This image was taken at an angle. The affected area is the arm. Male contributor, age 50–59:
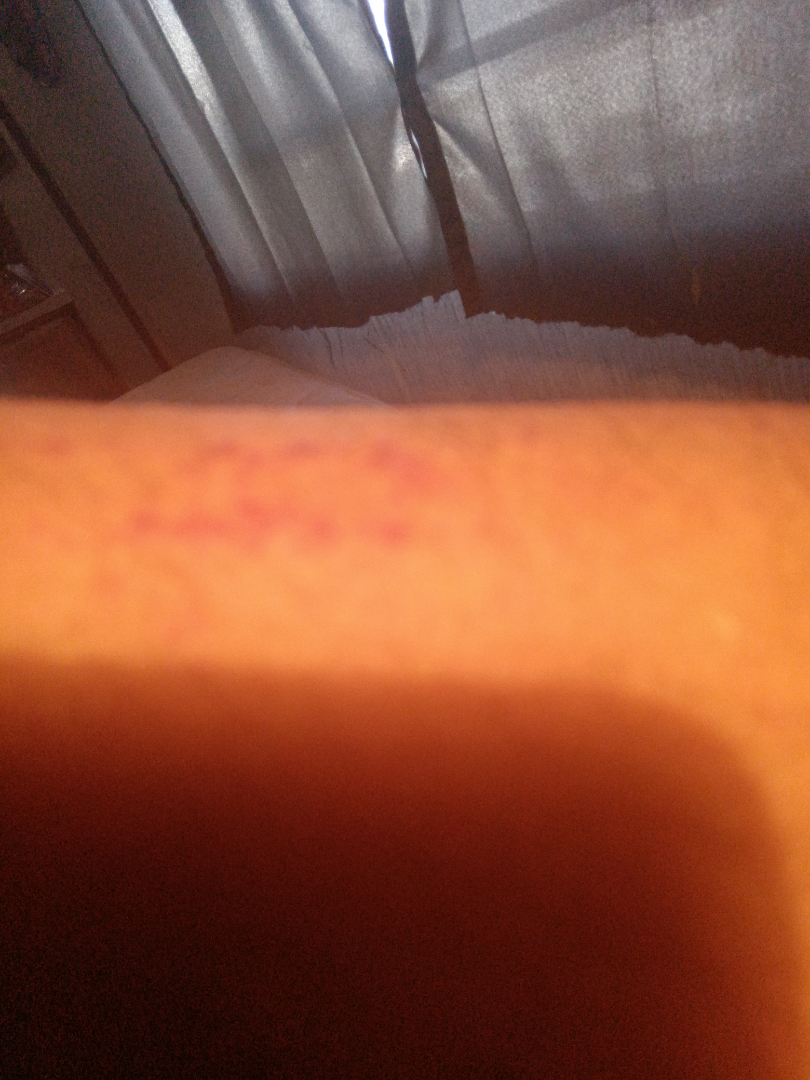The dermatologist could not determine a likely condition from the photograph alone.